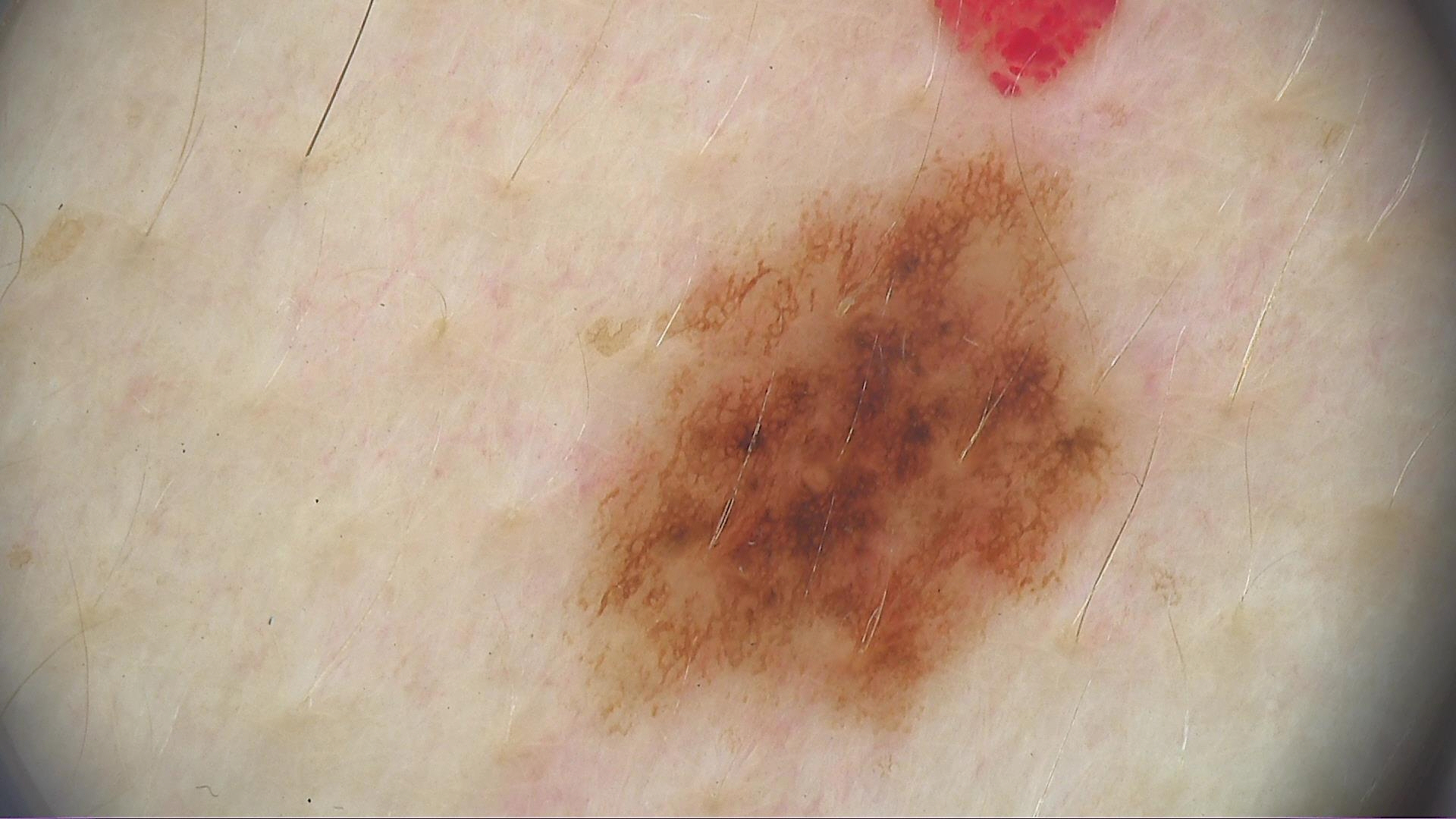Q: What is the imaging modality?
A: dermoscopy
Q: What was the diagnostic impression?
A: dysplastic compound nevus (expert consensus)